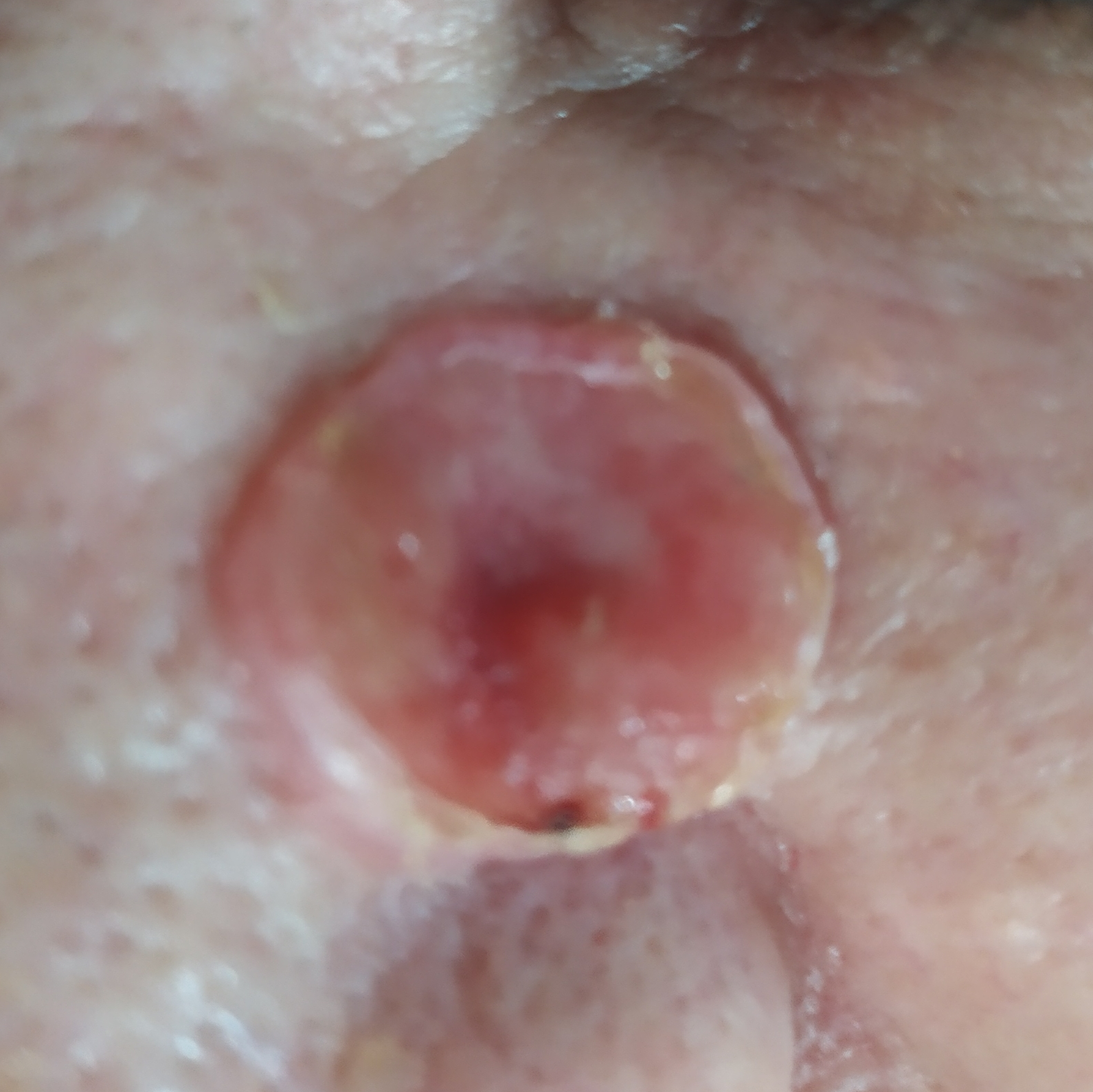History notes prior malignancy (patient or family) and prior skin cancer (patient or family). The patient was assessed as FST III. A clinical photograph of a skin lesion. The lesion is roughly 17 by 14 mm. Confirmed on histopathology as a malignancy — a basal cell carcinoma.